A skin lesion imaged with a dermatoscope; a male subject, aged around 20: 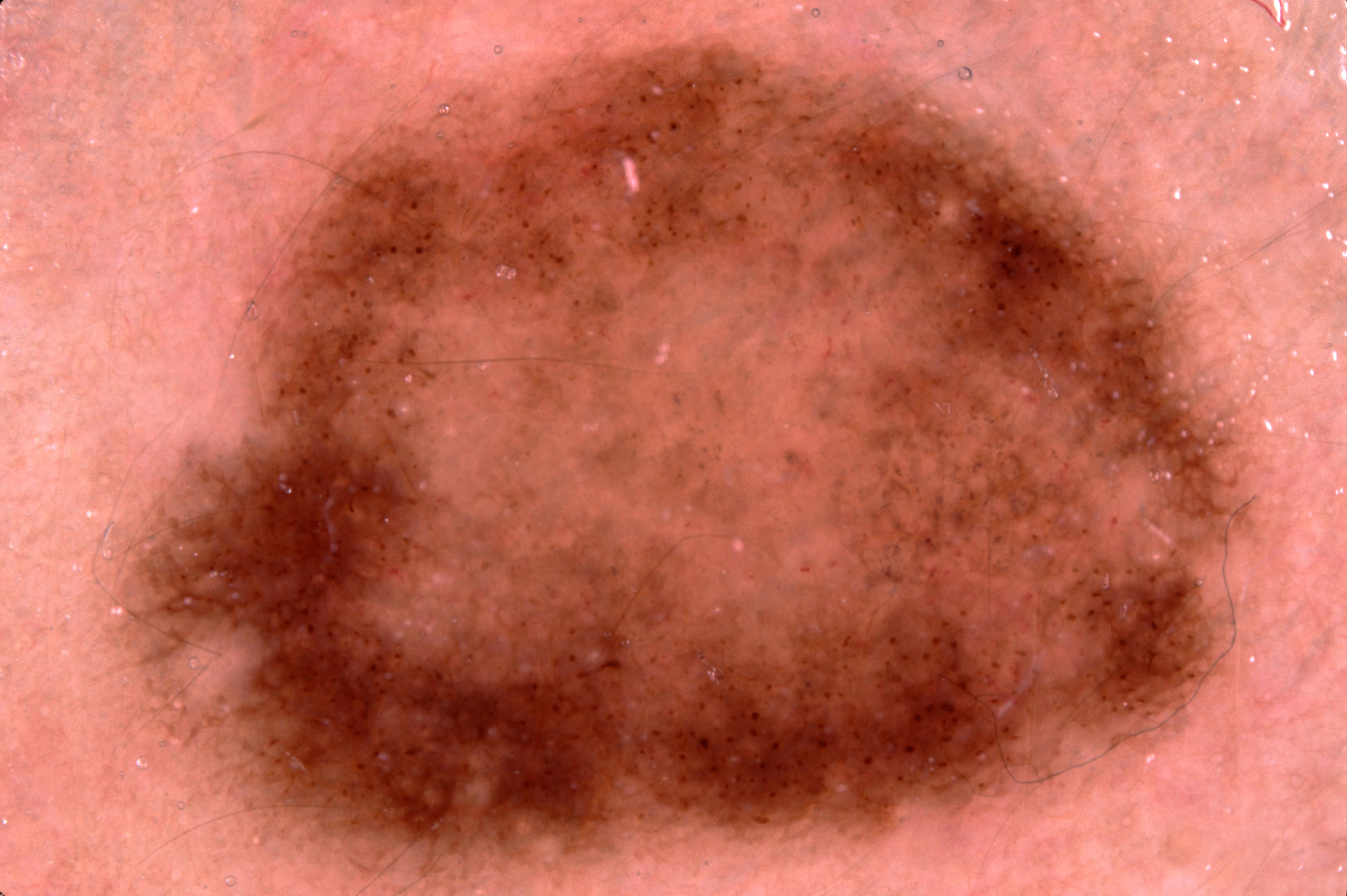The lesion covers approximately 61% of the dermoscopic field.
Dermoscopy demonstrates pigment network; no streaks, milia-like cysts, or negative network.
The lesion is bounded by x1=100 y1=33 x2=1266 y2=895.
The lesion runs off the edge of the field of view.
Diagnosed as a melanocytic nevus.